A dermatoscopic image of a skin lesion.
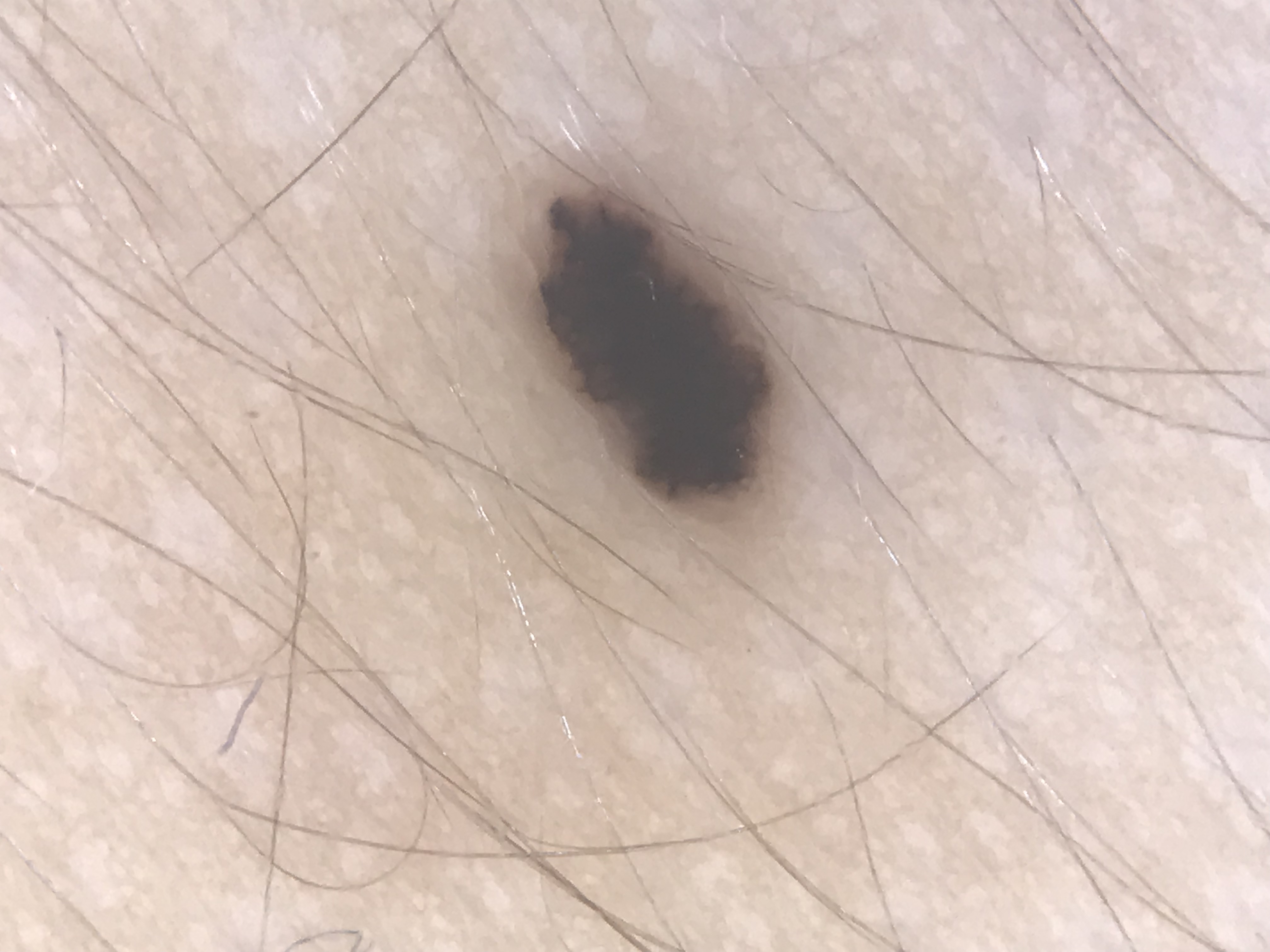Consistent with a benign lesion — a dysplastic junctional nevus.